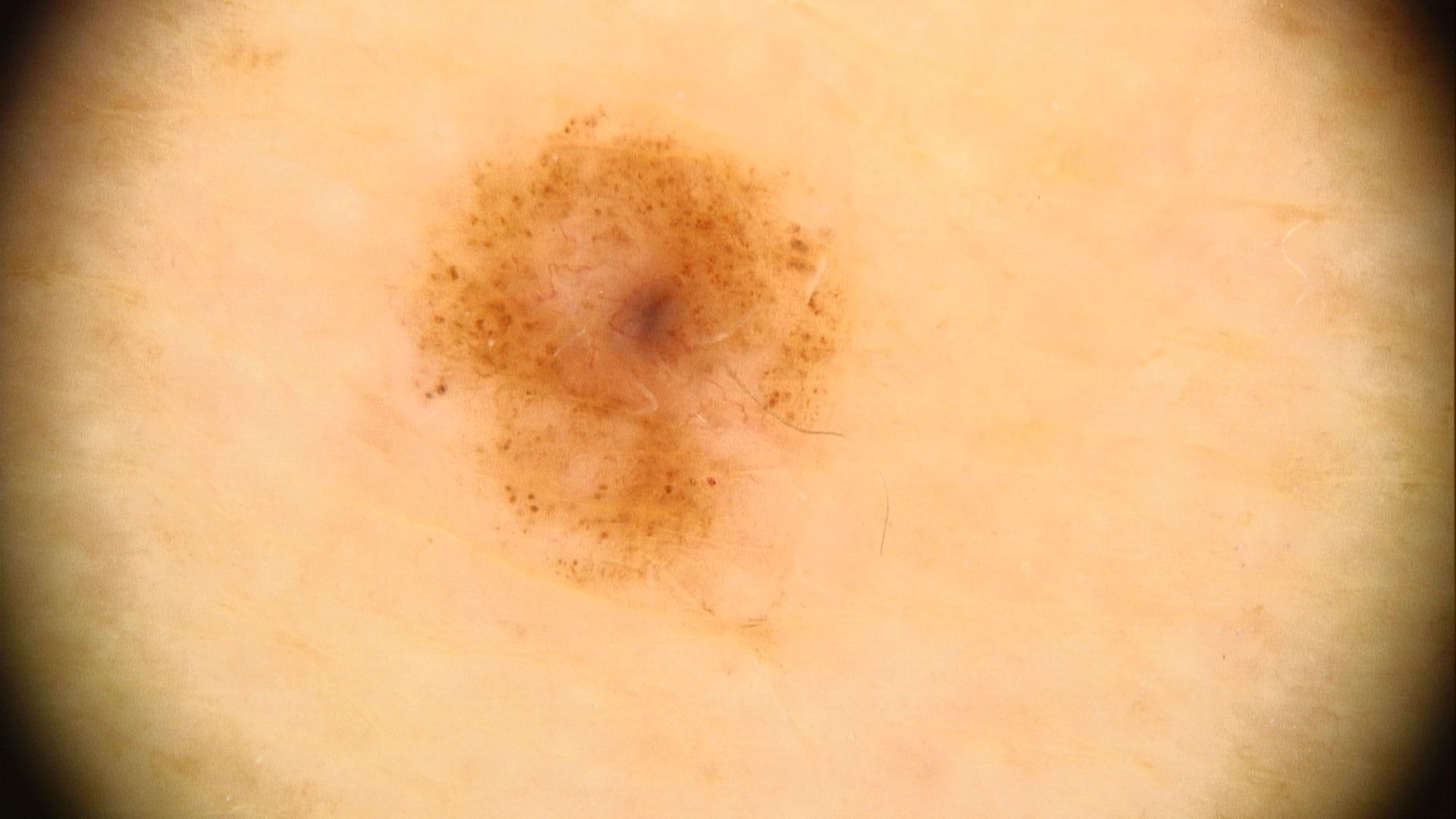Case summary: A female patient in their mid-70s. A dermoscopy image of a single skin lesion. The patient was assessed as Fitzpatrick phototype II. The lesion is on an upper extremity. Diagnosis: Confirmed on histopathology as a lesion of melanocytic origin — a nevus.